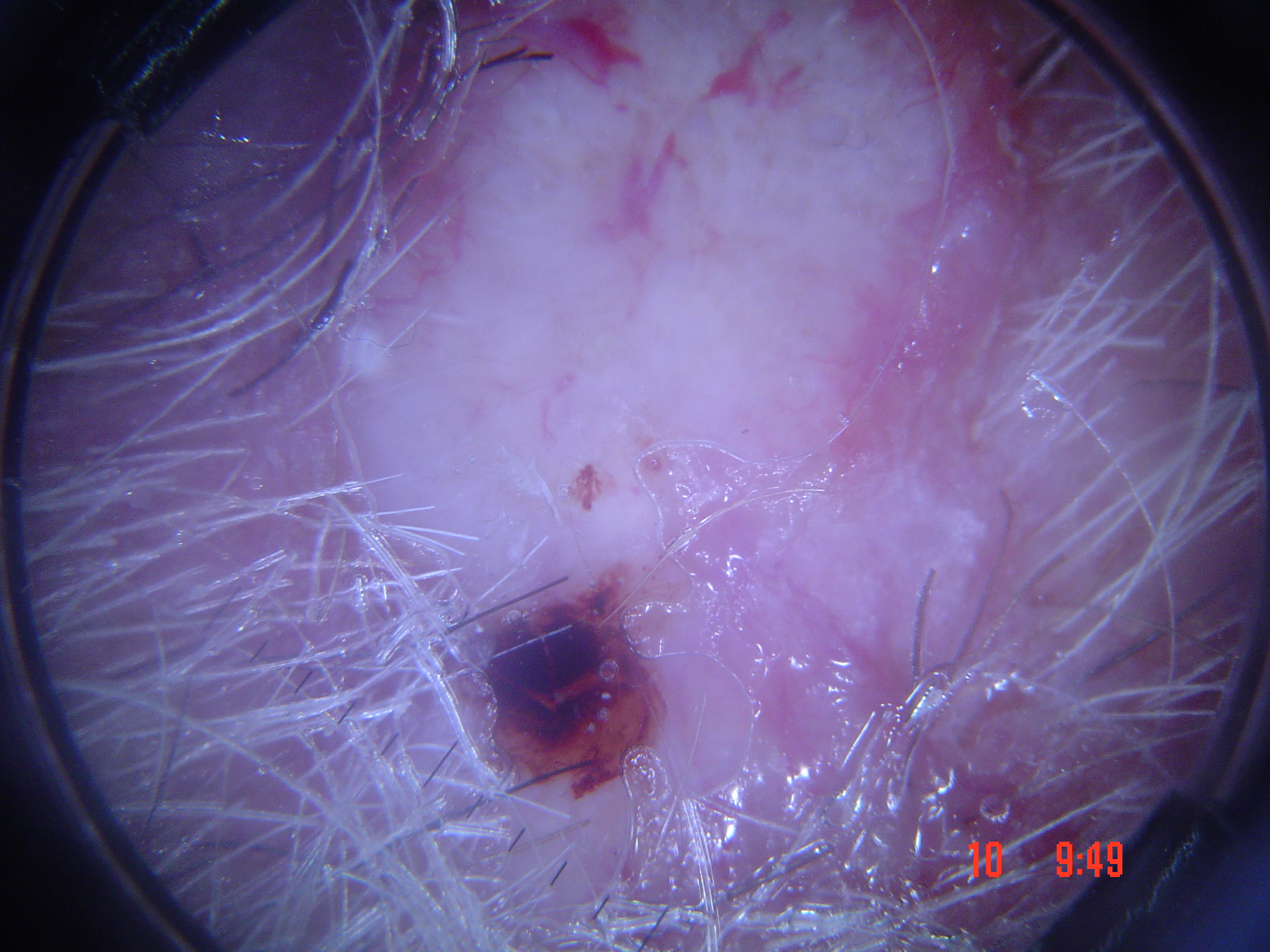A dermoscopic image of a skin lesion. Histopathologically confirmed as a malignant lesion — a basal cell carcinoma.